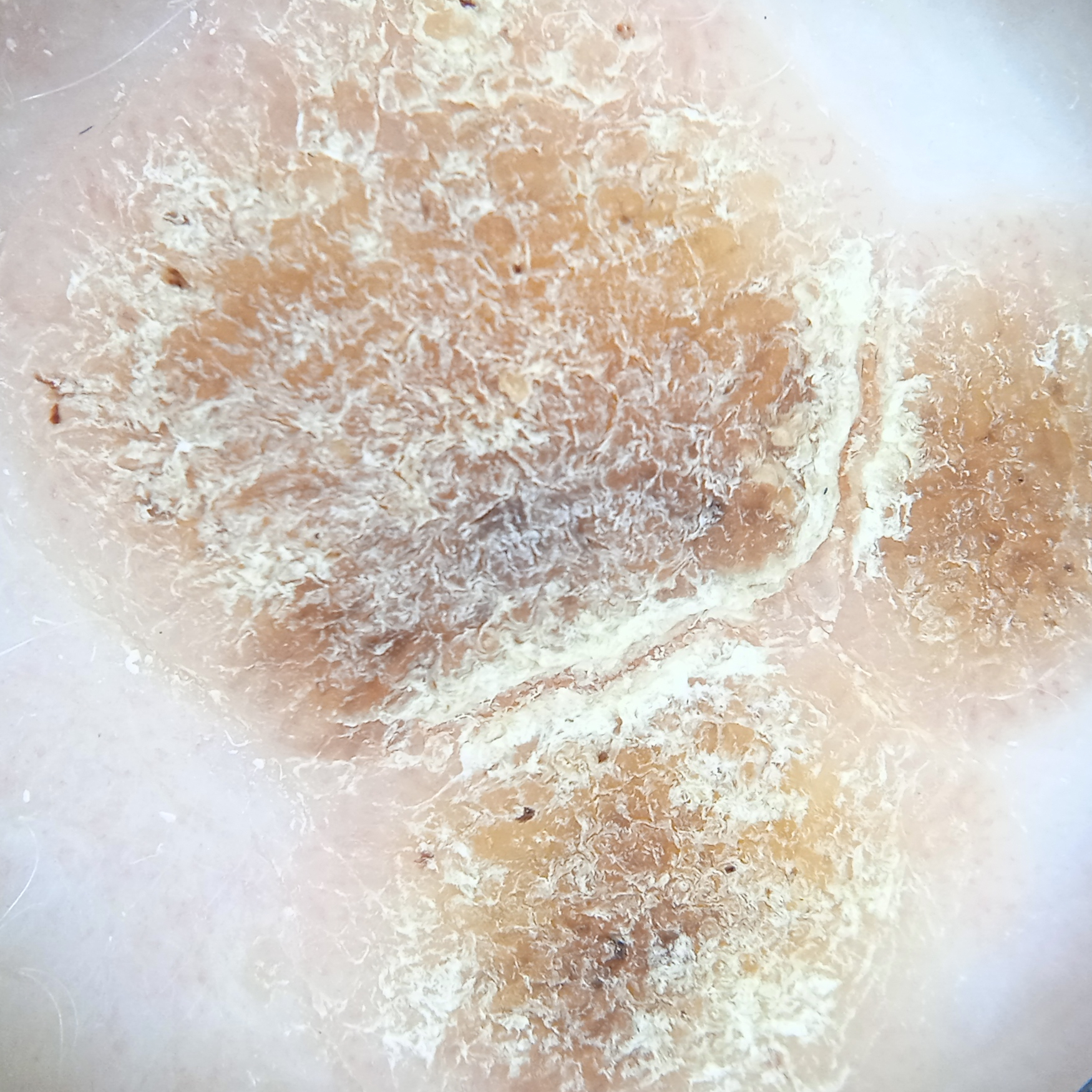Conclusion: The diagnostic impression was a seborrheic keratosis.